A skin lesion imaged with a dermatoscope.
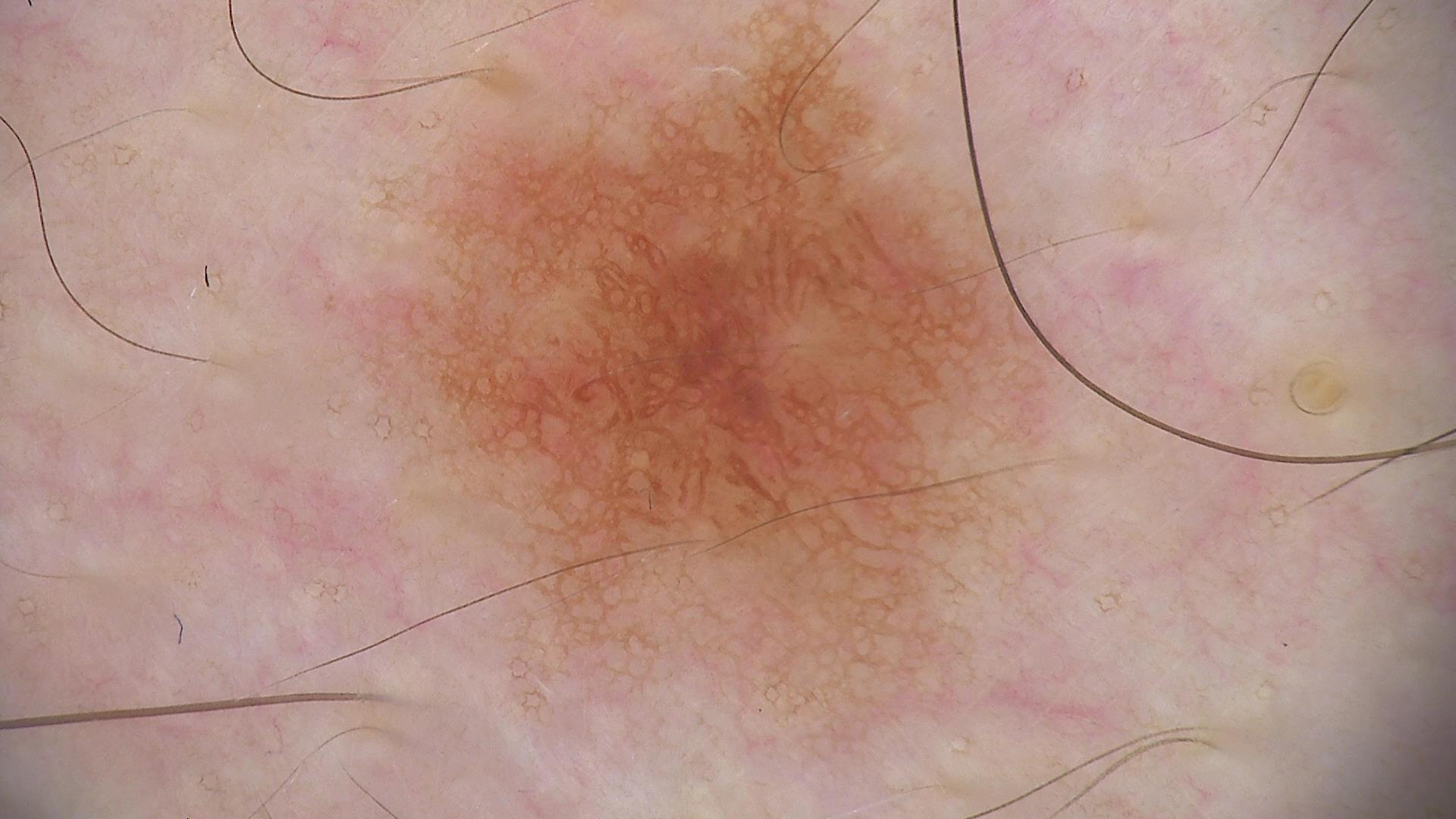<dermoscopy>
<diagnosis>
<name>dysplastic junctional nevus</name>
<code>jd</code>
<malignancy>benign</malignancy>
<super_class>melanocytic</super_class>
<confirmation>expert consensus</confirmation>
</diagnosis>
</dermoscopy>